A dermoscopy image of a single skin lesion.
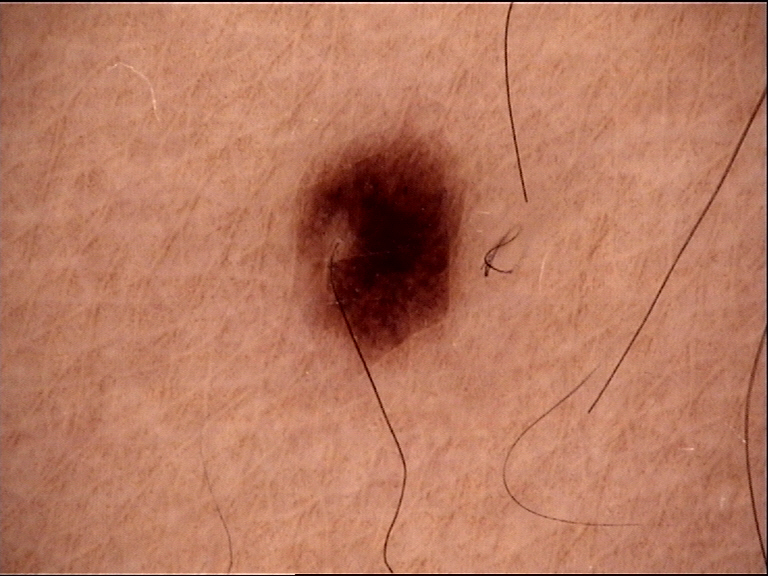Impression: Classified as a banal lesion — a junctional nevus.